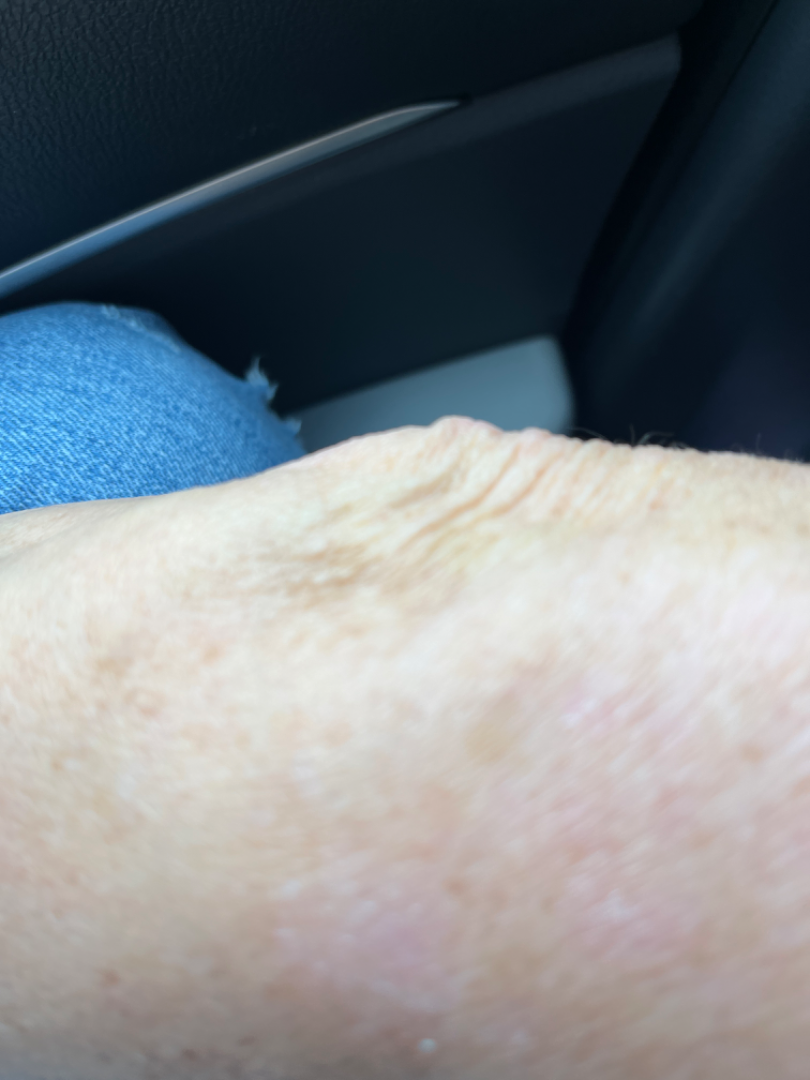Q: Anatomic location?
A: arm
Q: Image view?
A: close-up
Q: What is the dermatologist's impression?
A: Eczema (leading)